The photograph was taken at an angle. Located on the arm, front of the torso and back of the torso:
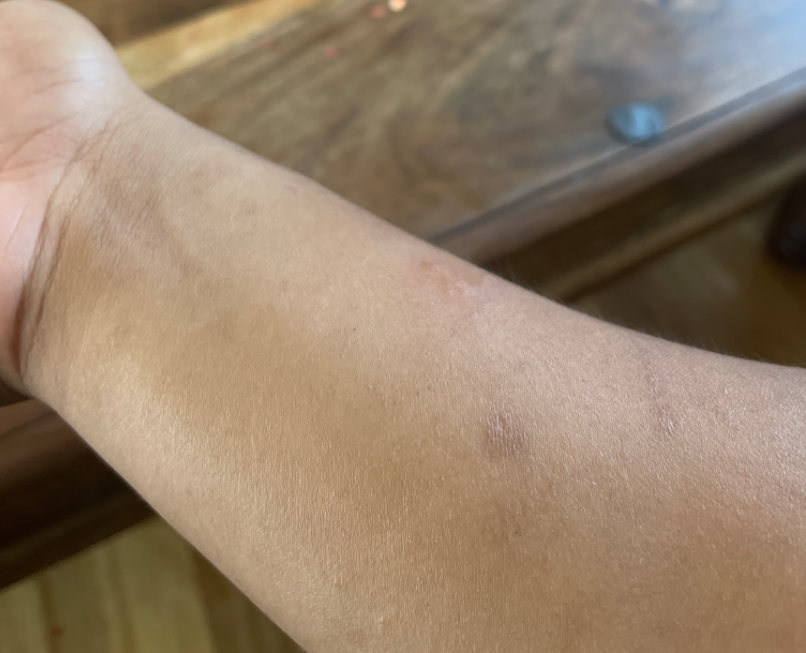Notes:
– assessment — ungradable on photographic review
– surface texture — raised or bumpy
– lesion symptoms — bothersome appearance and itching
– self-categorized as — a rash
– associated systemic symptoms — fatigue
– onset — less than one week